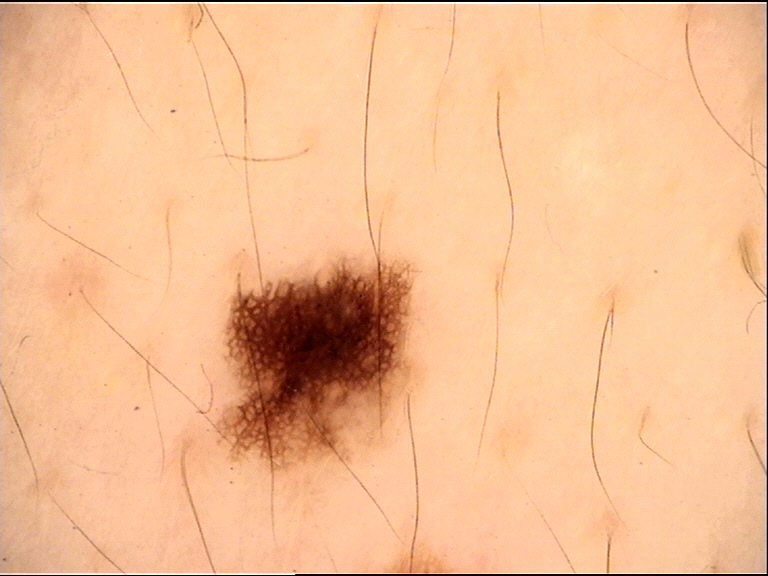image type: dermoscopy | assessment: dysplastic junctional nevus (expert consensus).